A skin lesion imaged with a dermatoscope. A female patient 60 years of age. Acquired for a research image collection, with no referral diagnosis: 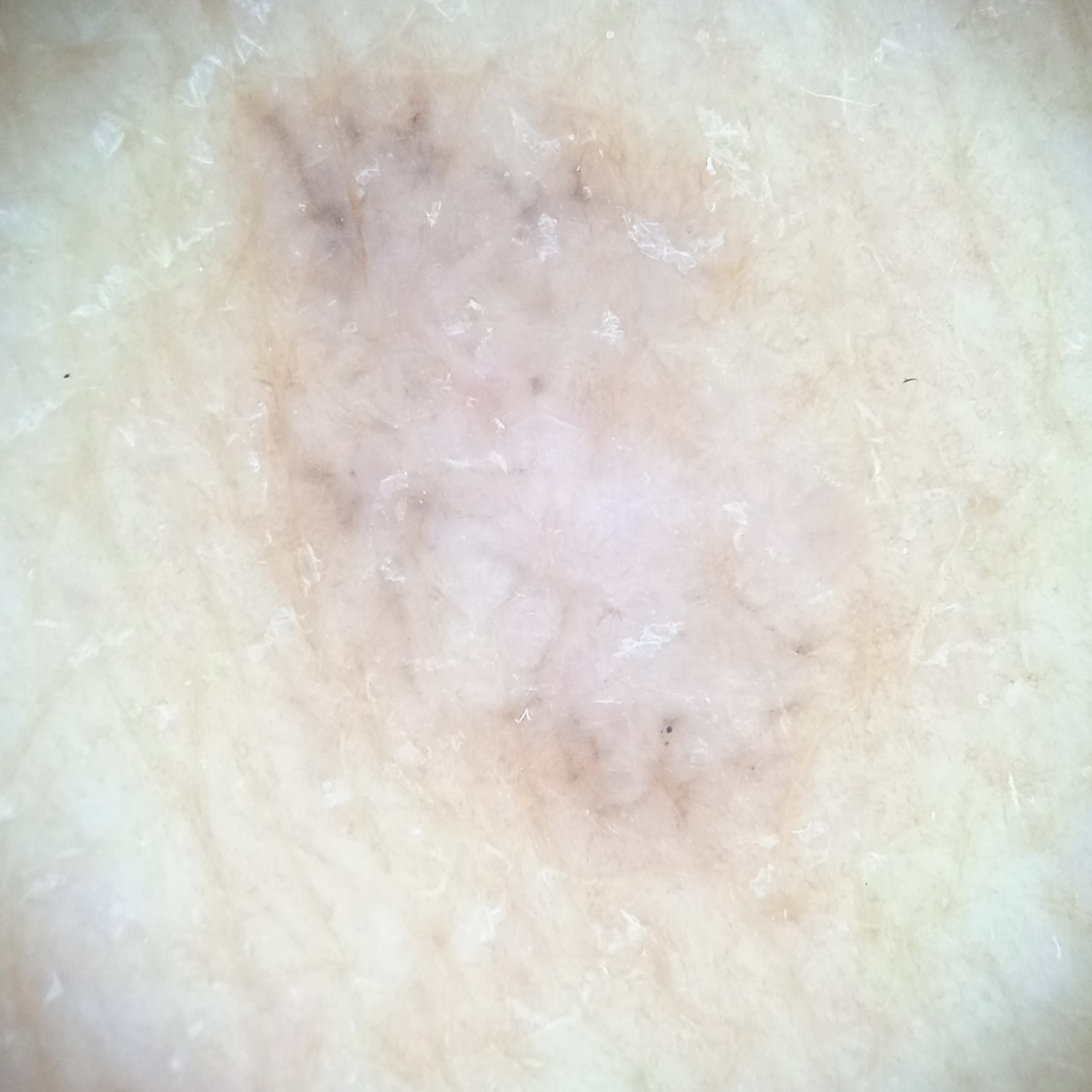Q: Where is the lesion?
A: the back
Q: How large is the lesion?
A: 10.4 mm
Q: What was the diagnosis?
A: basal cell carcinoma (dermatologist consensus)